A female patient age 61; the chart records pesticide exposure, prior malignancy (patient or family), and prior skin cancer (patient or family); recorded as skin type II; a clinical photograph showing a skin lesion: 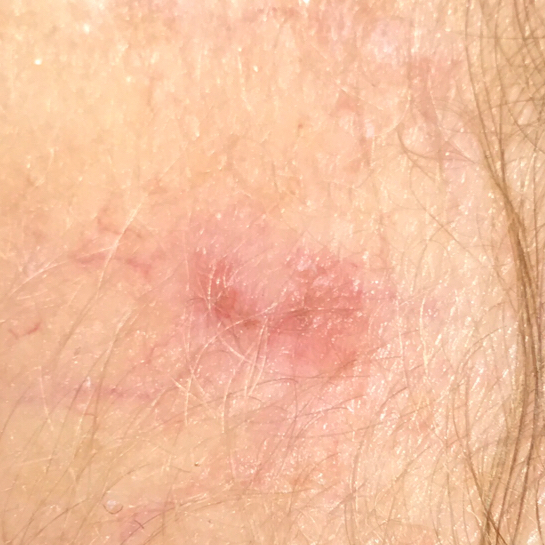Case summary:
The lesion was found on an ear. Measuring about 9 × 6 mm. The patient reports that the lesion is not elevated and does not hurt.
Diagnosis:
Histopathological examination showed a squamous cell carcinoma.